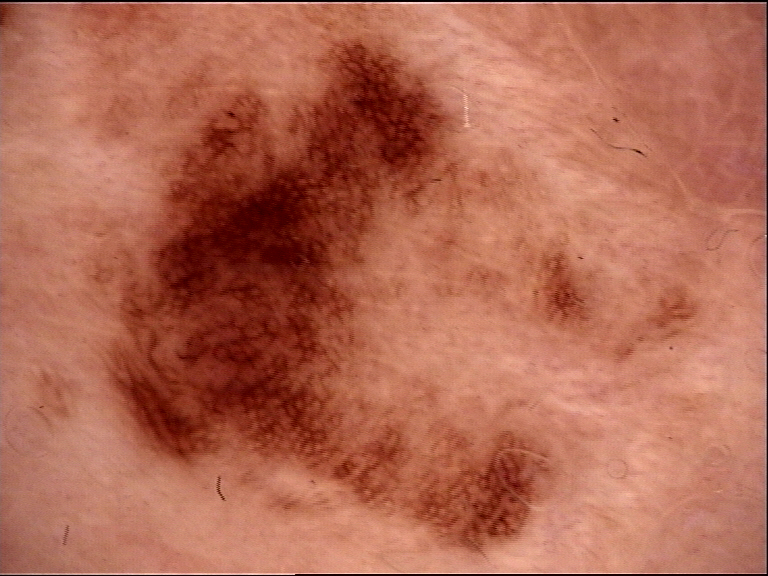image type: dermoscopy; classification: dysplastic; diagnostic label: recurrent nevus (expert consensus).